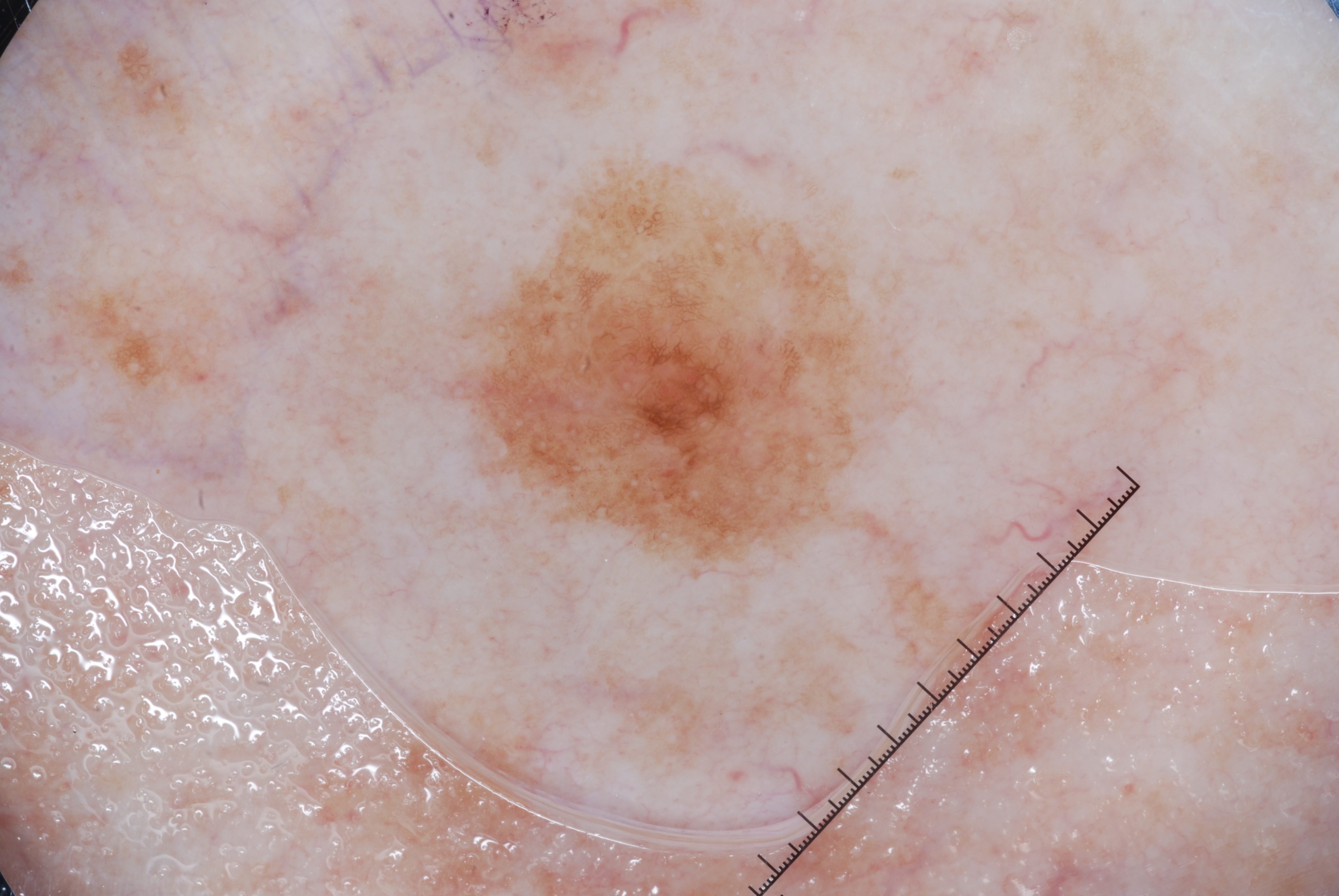A dermoscopy image of a single skin lesion. A male patient approximately 60 years of age. On dermoscopy, the lesion shows pigment network. A mid-sized lesion within the field. The visible lesion spans left=448, top=165, right=871, bottom=565. Diagnosed as a melanocytic nevus.